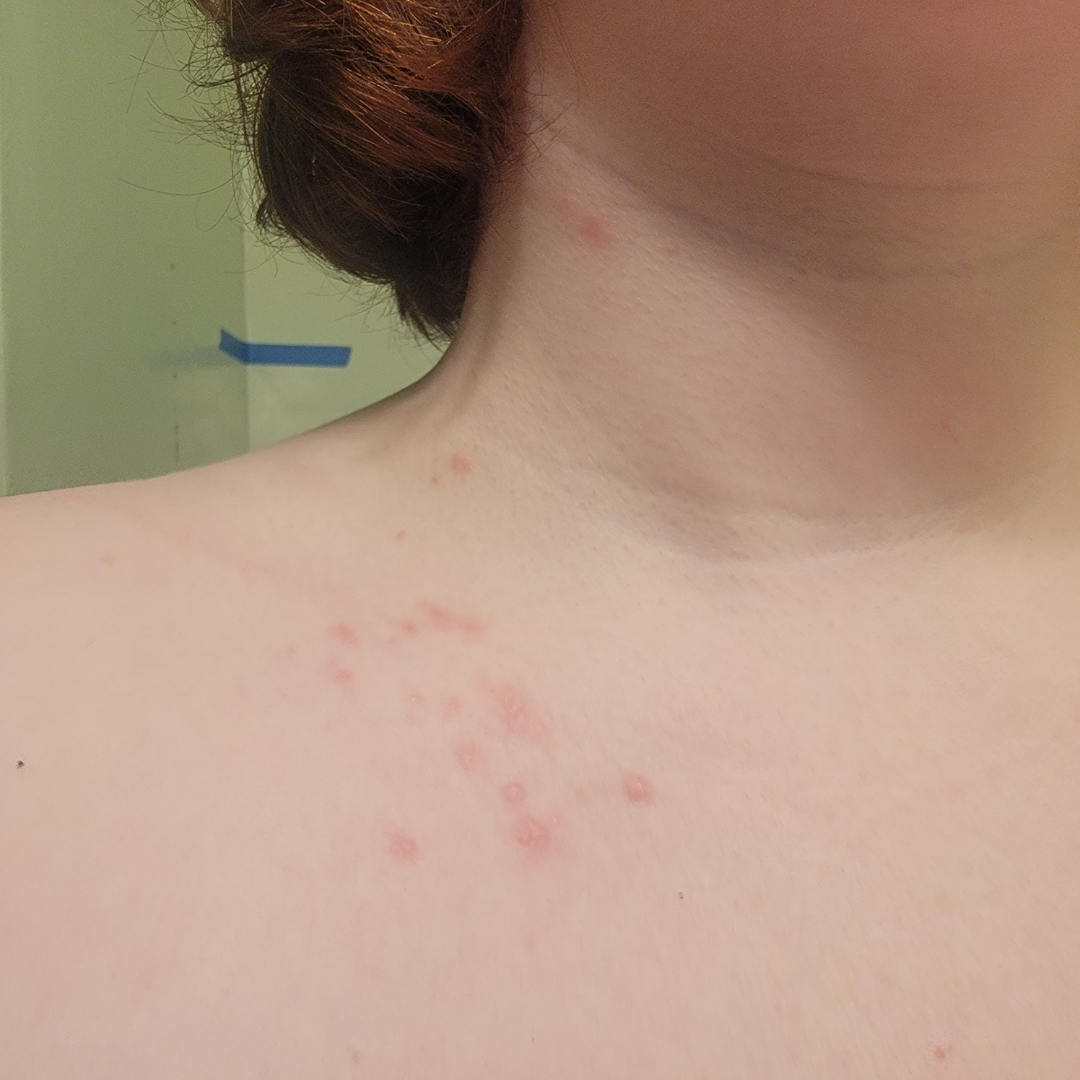{"assessment": "indeterminate", "texture": "raised or bumpy", "body_site": ["head or neck", "front of the torso"], "patient_category": "acne", "shot_type": "at a distance", "patient": "female, age 18–29"}